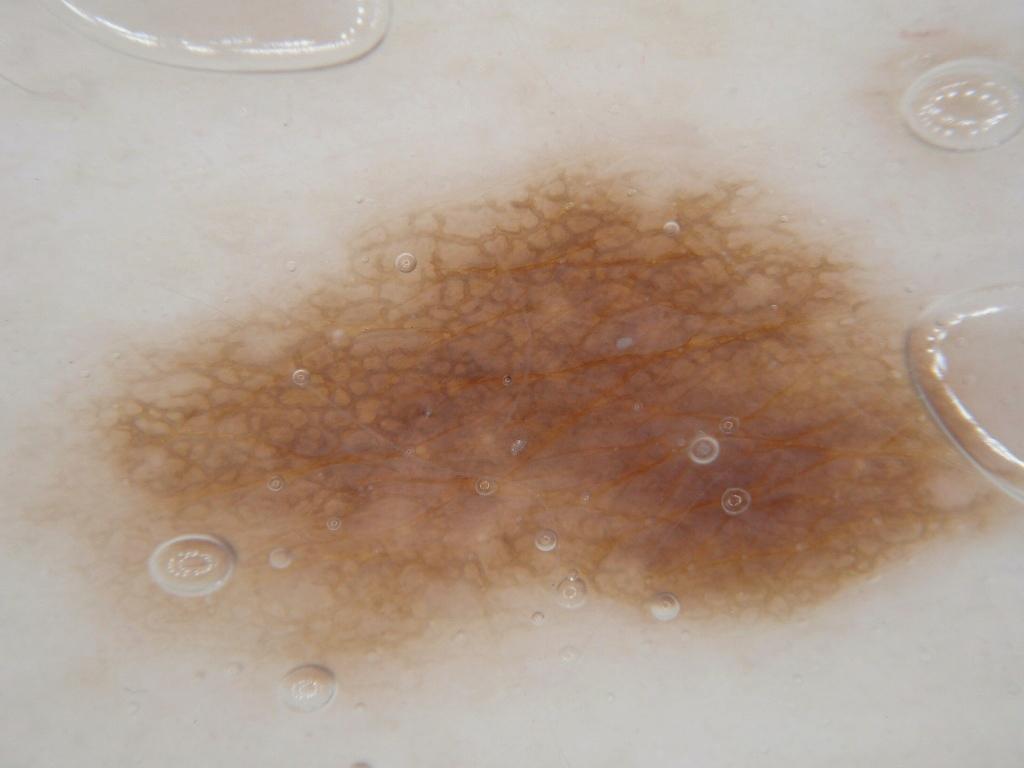Q: What is the imaging modality?
A: dermatoscopic image of a skin lesion
Q: Who is the patient?
A: female, in their mid-40s
Q: Where is the lesion in the image?
A: [4, 139, 1022, 737]
Q: Which dermoscopic features were noted?
A: pigment network; absent: milia-like cysts, negative network, globules, and streaks
Q: What is this lesion?
A: a melanocytic nevus